The patient is a male approximately 75 years of age; a skin lesion imaged with a dermatoscope — 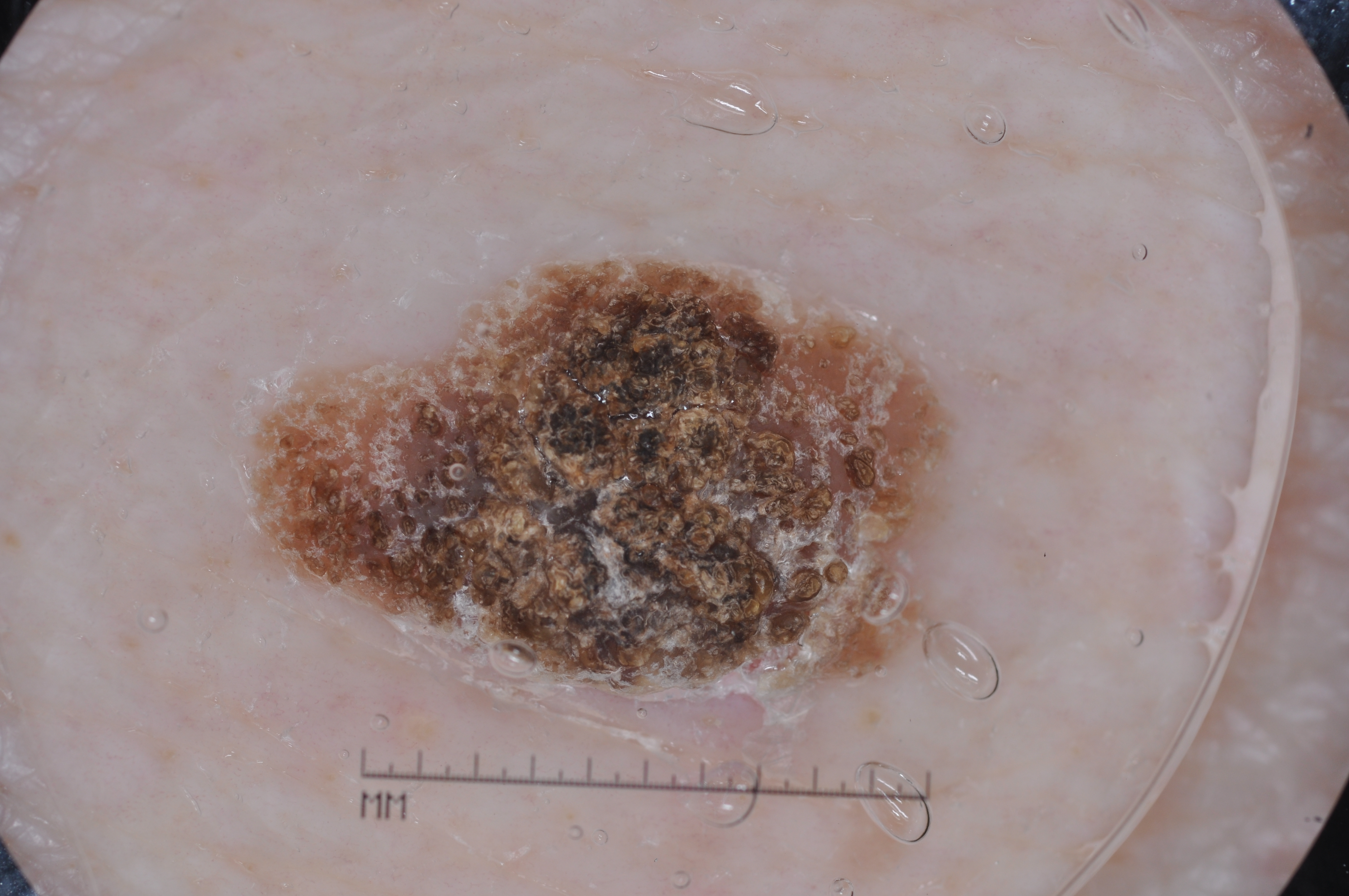The lesion covers approximately 17% of the dermoscopic field. Dermoscopy demonstrates milia-like cysts; no pigment network, streaks, or negative network. In (x1, y1, x2, y2) order, the lesion is bounded by box(263, 266, 948, 679). The lesion was assessed as a seborrheic keratosis, a non-melanocytic (keratinocytic) lesion.